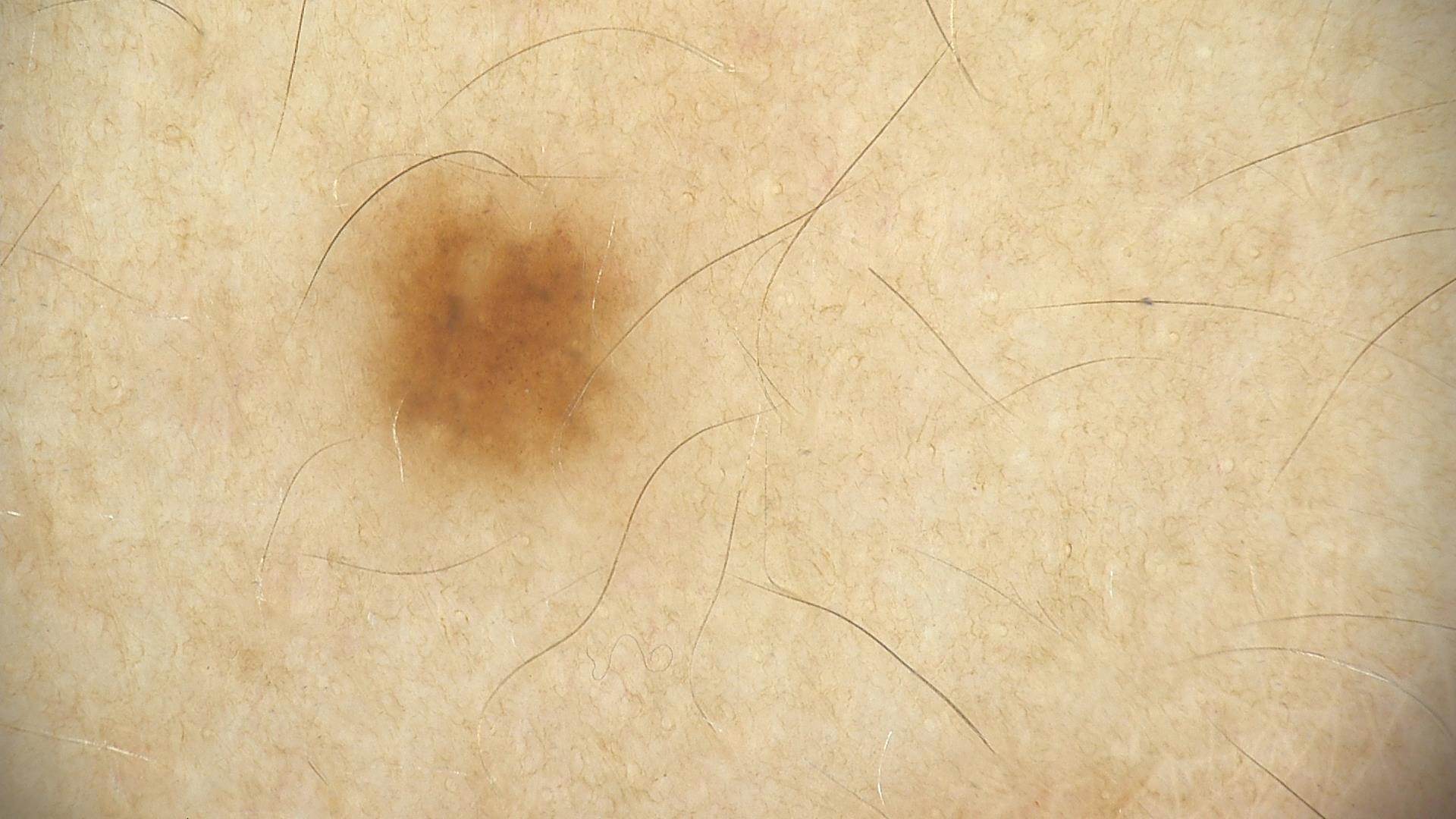A dermoscopic close-up of a skin lesion.
Labeled as a benign lesion — a dysplastic junctional nevus.